A dermoscopy image of a single skin lesion.
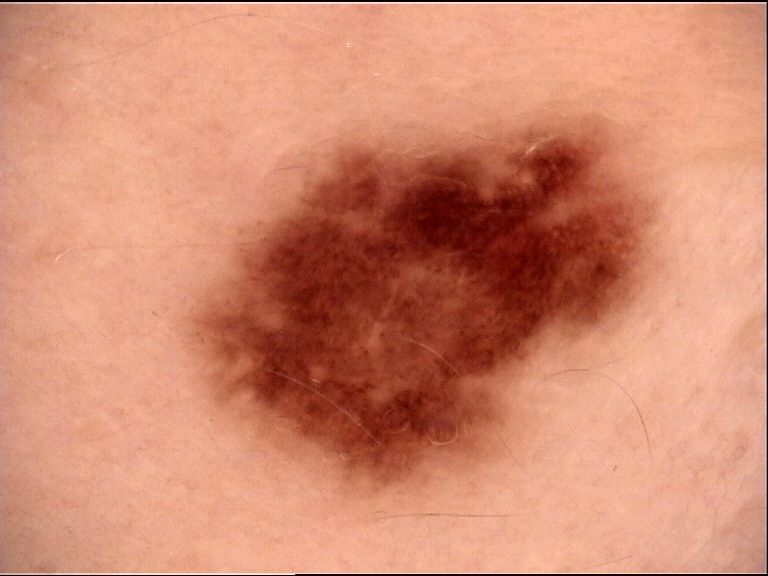– diagnostic label: dysplastic compound nevus (expert consensus)